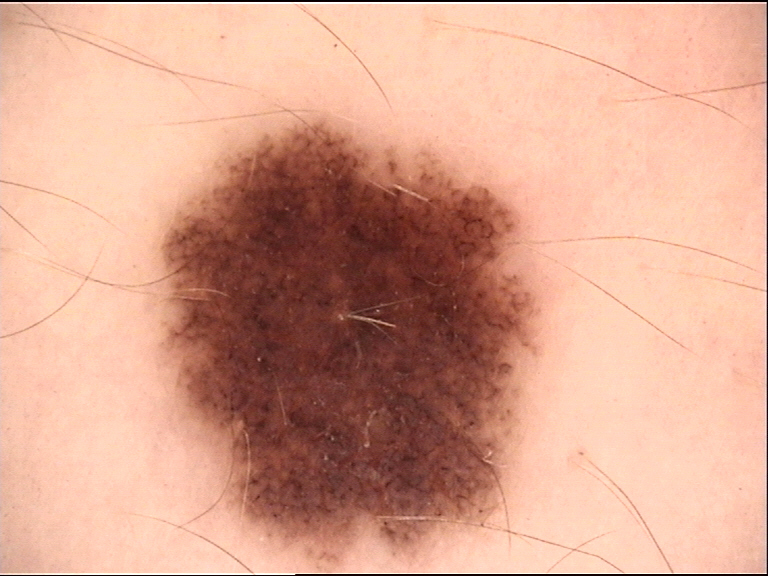Impression:
The diagnosis was a benign lesion — a dysplastic junctional nevus.